A dermoscopy image of a single skin lesion:
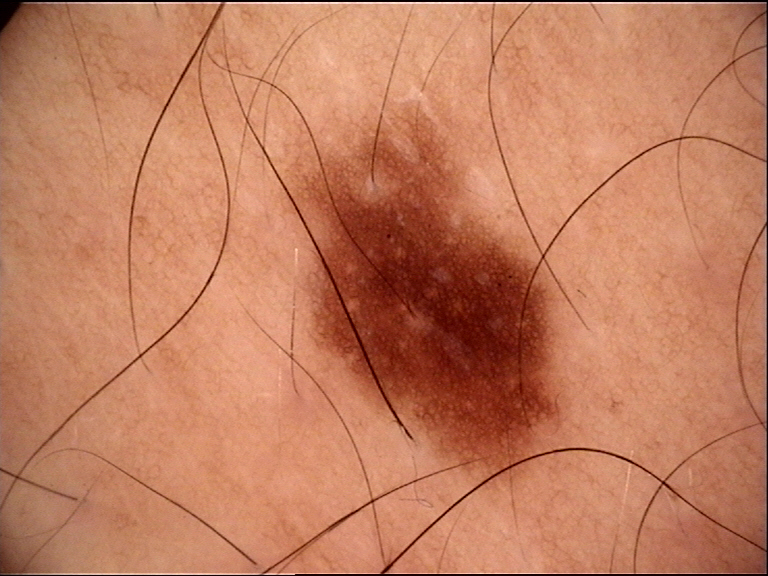| feature | finding |
|---|---|
| classification | banal |
| assessment | junctional nevus (expert consensus) |